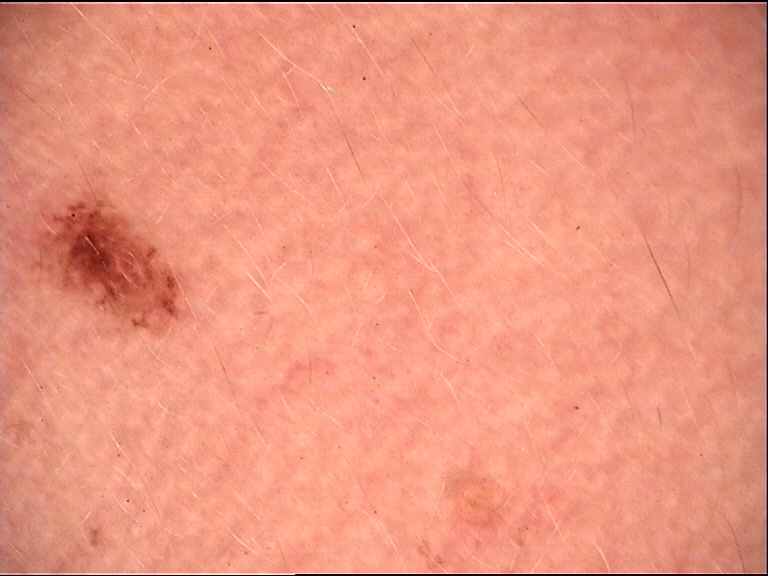Dermoscopy of a skin lesion. Diagnosed as a dysplastic junctional nevus.